This is a close-up image; the contributor is 18–29, male.
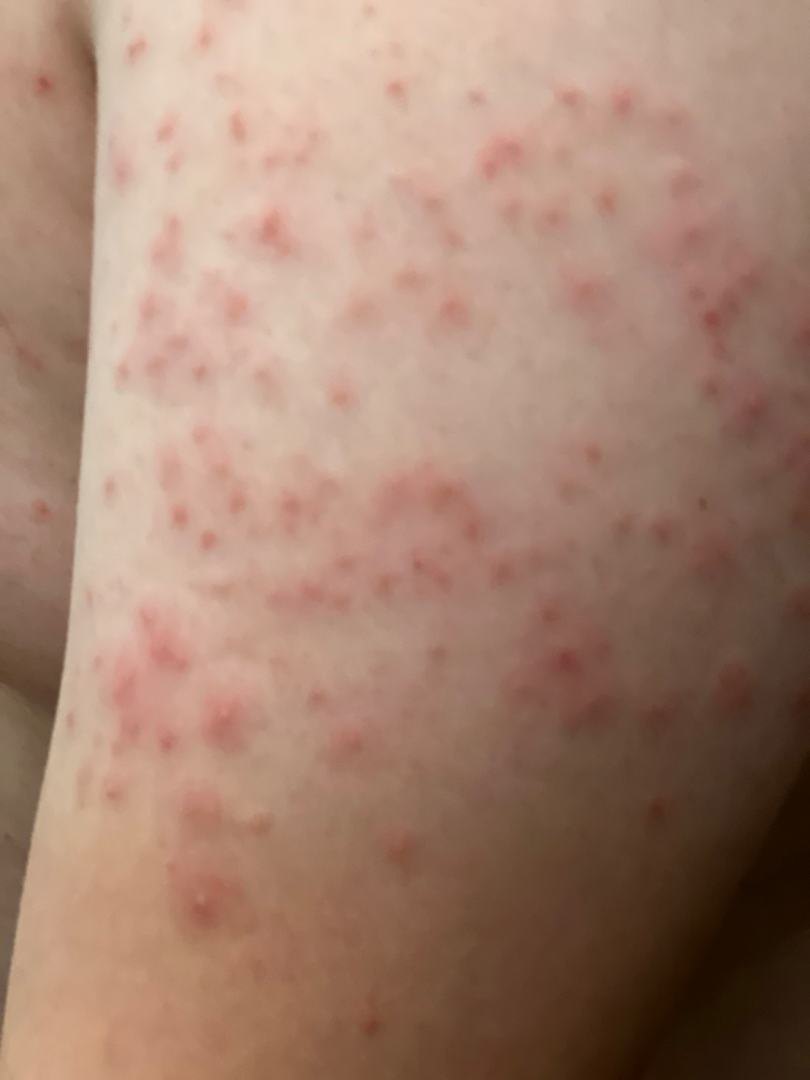The reviewing dermatologist was unable to assign a differential diagnosis from the image.